A skin lesion imaged with a dermatoscope:
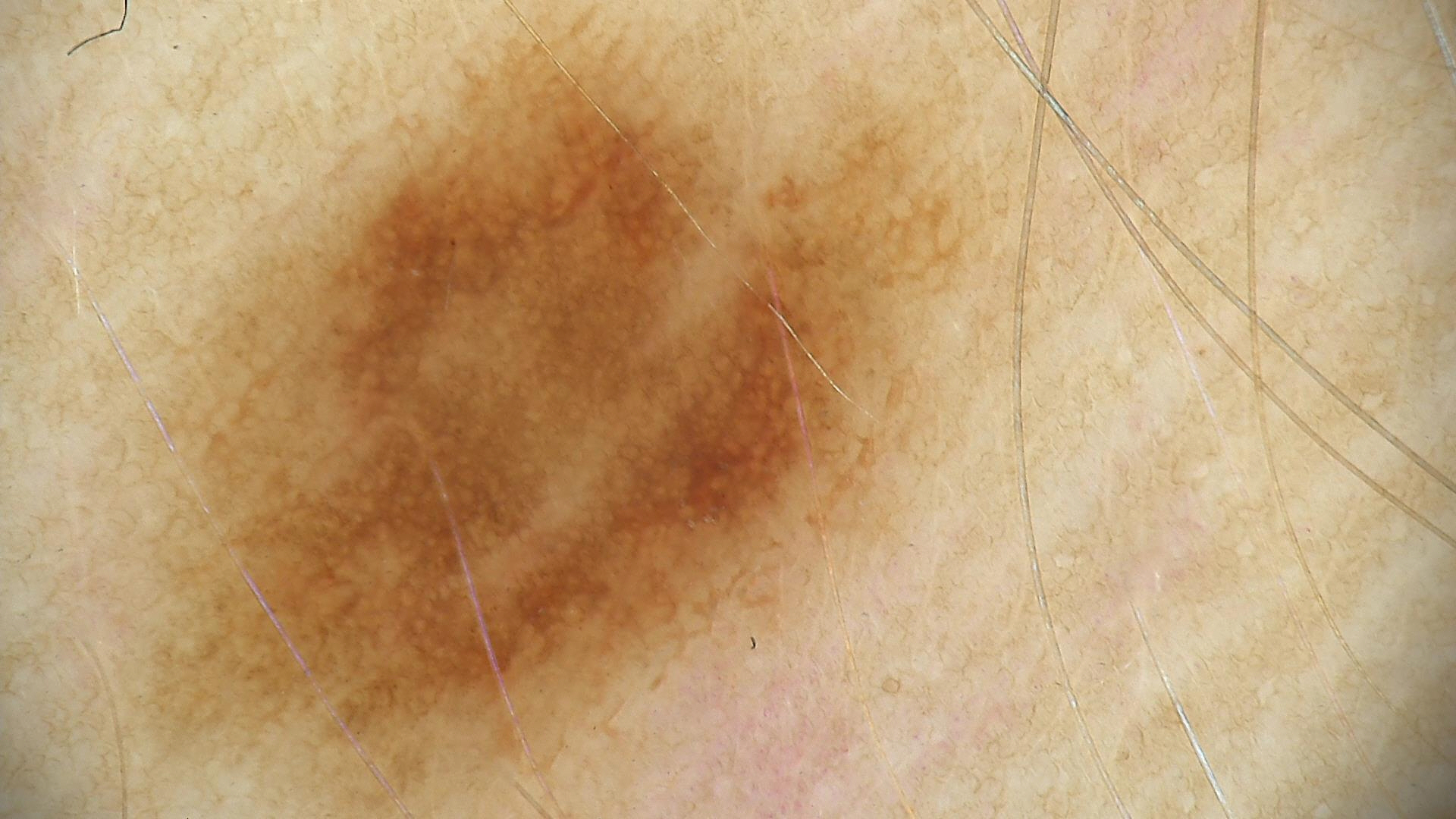The diagnostic label was a benign lesion — a dysplastic junctional nevus.